A dermoscopic photograph of a skin lesion.
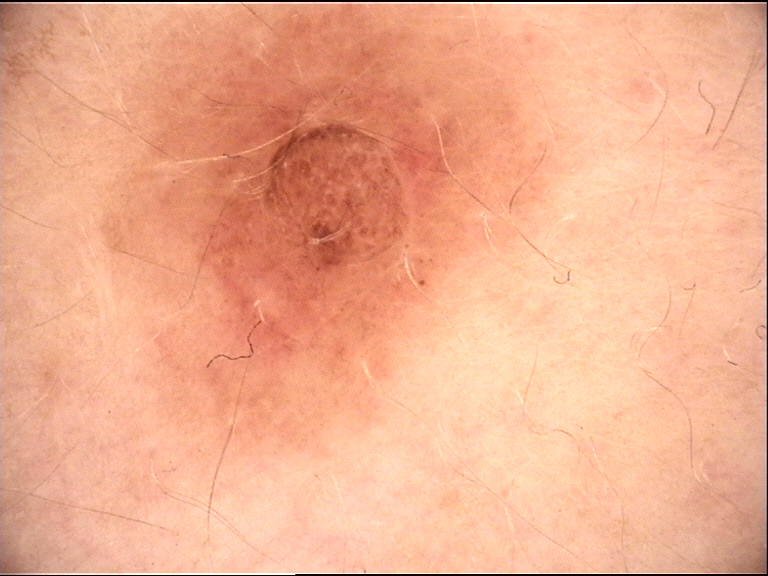Findings:
The morphology is that of a banal lesion.
Impression:
Labeled as a dermal nevus.